A clinical photograph of a skin lesion; the patient is Fitzpatrick IV — 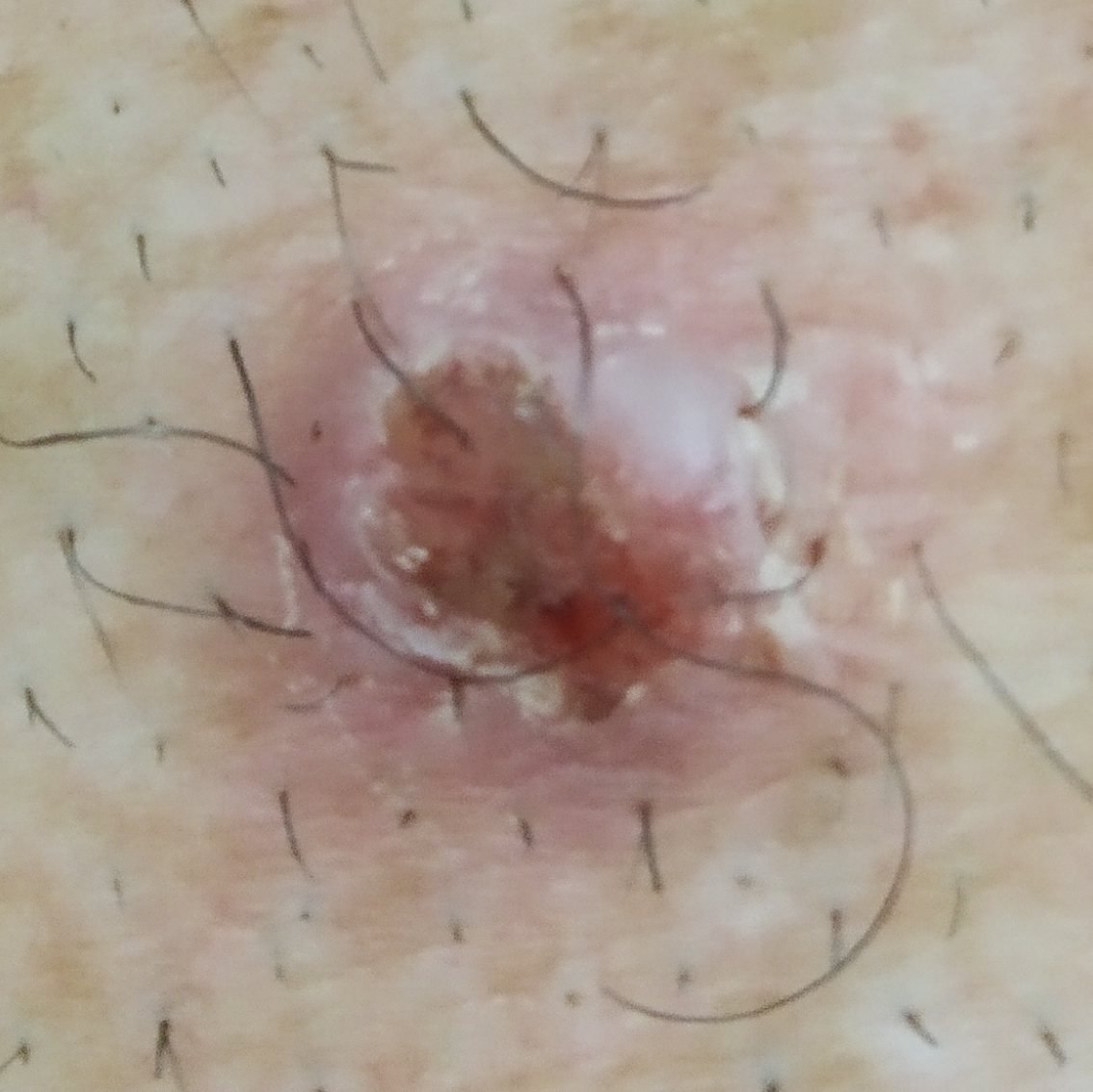{
  "lesion_size": {
    "diameter_1_mm": 1.0,
    "diameter_2_mm": 1.0
  },
  "diagnosis": {
    "name": "basal cell carcinoma",
    "code": "BCC",
    "malignancy": "malignant",
    "confirmation": "histopathology"
  }
}